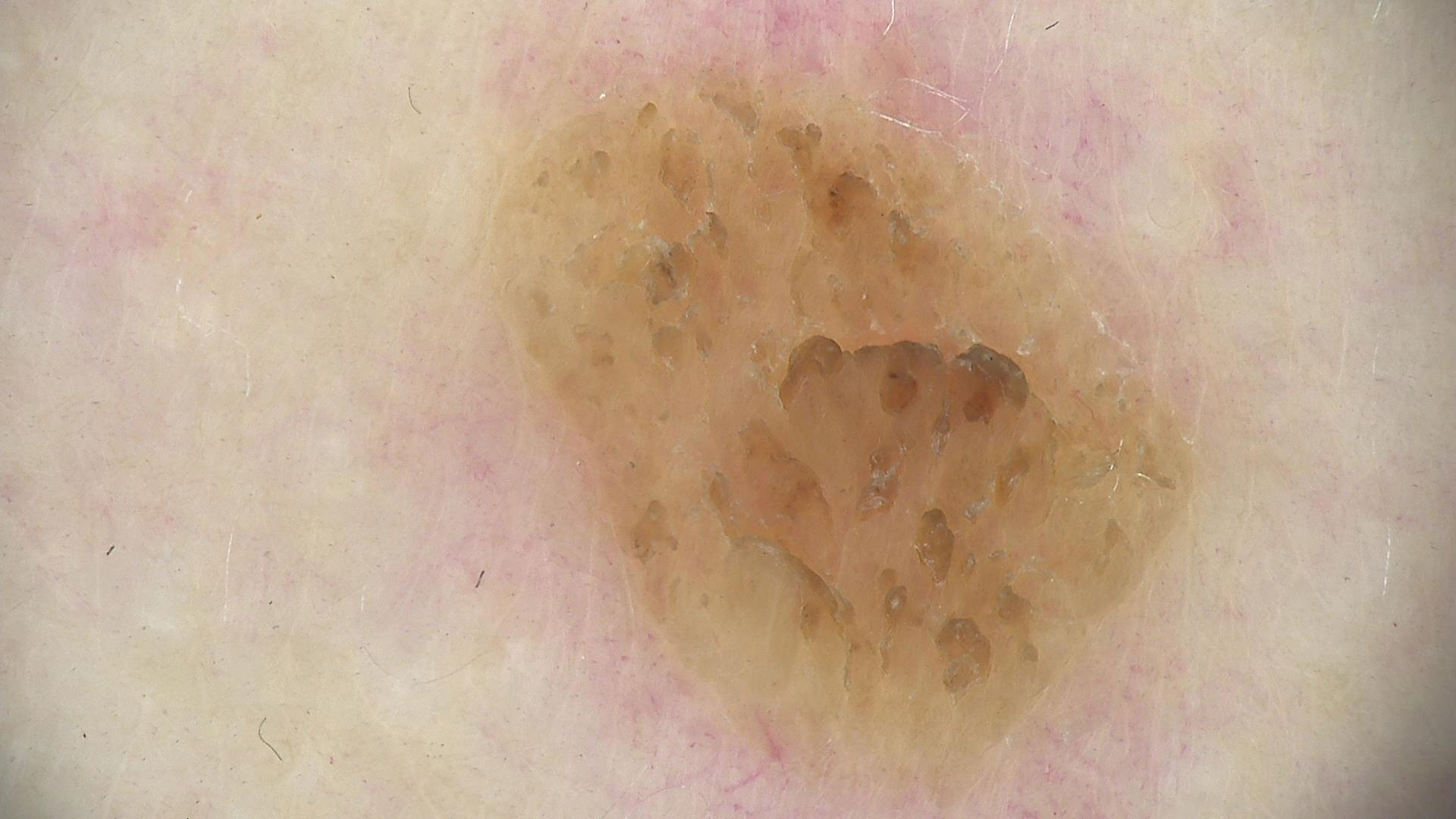Findings: This is a keratinocytic lesion. Conclusion: Consistent with a benign lesion — a seborrheic keratosis.